The patient is a female aged 50–59 · the photo was captured at an angle · located on the leg: 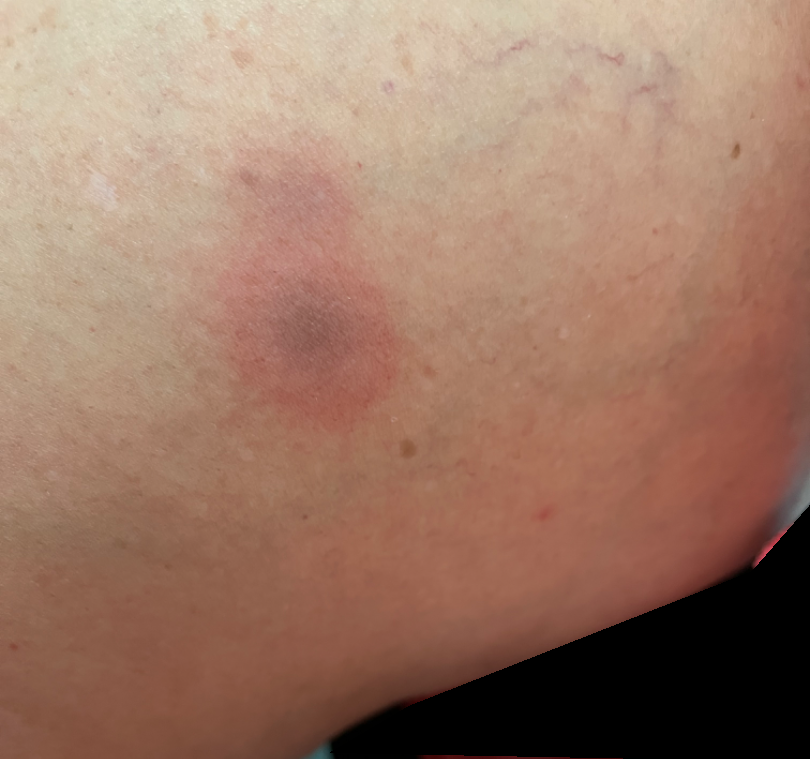Clinical context: The patient indicates the condition has been present for one to three months. The patient also reports fatigue. Skin tone: Fitzpatrick III; human graders estimated a Monk skin tone scale of 4. The lesion is described as flat. Assessment: Most consistent with Geographic tongue; also on the differential is Insect Bite; a more distant consideration is Erythema multiforme.